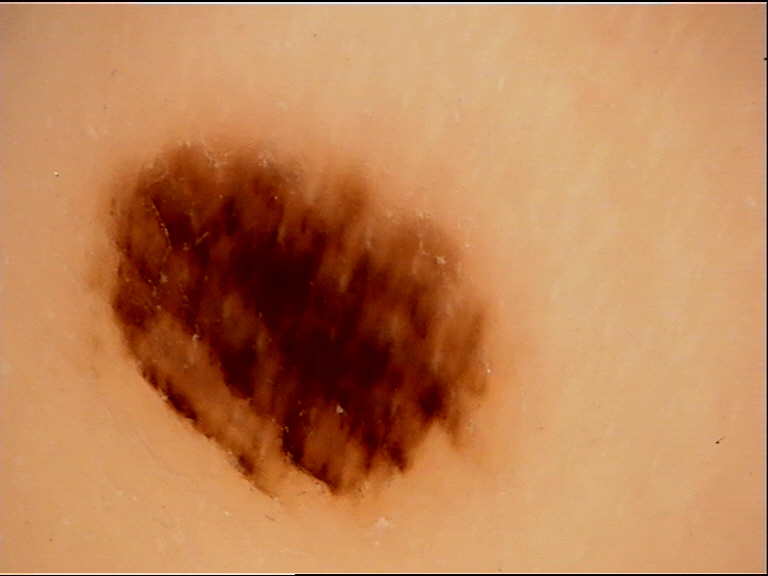assessment=acral junctional nevus (expert consensus).